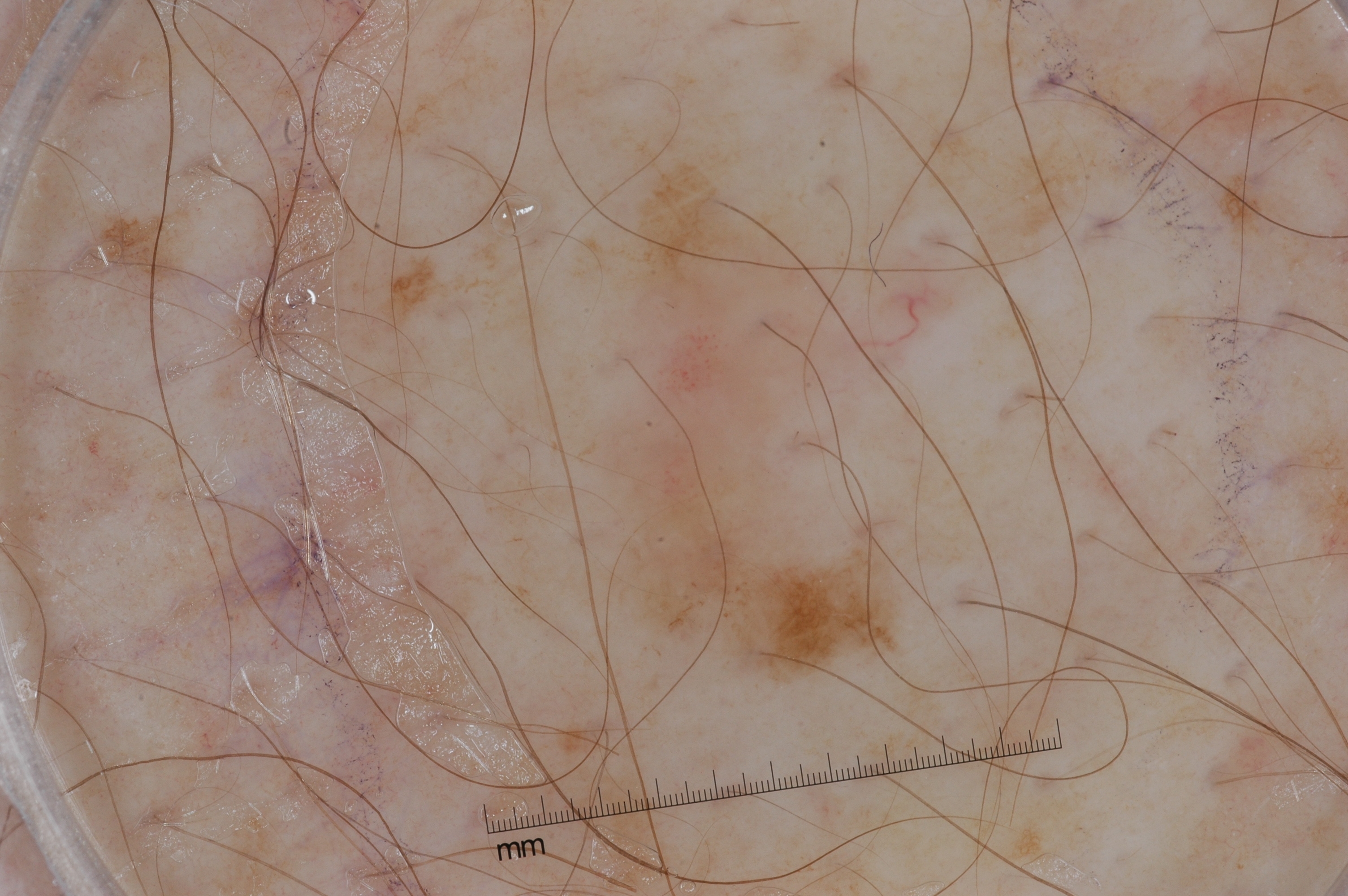| feature | finding |
|---|---|
| image | dermoscopy |
| patient | female, aged approximately 60 |
| lesion location | [537,158,982,713] |
| lesion extent | moderate |
| dermoscopic pattern | pigment network and milia-like cysts |
| impression | a melanoma |